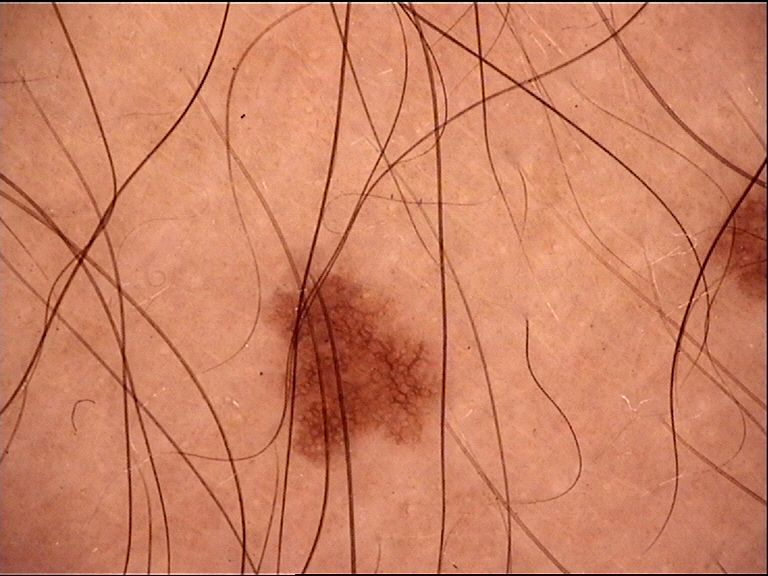Conclusion: Diagnosed as a banal lesion — a junctional nevus.